The contributor is male · the affected area is the arm and back of the hand · the contributor reports burning, bleeding, enlargement, darkening, itching, pain and bothersome appearance · the patient described the issue as a growth or mole · self-reported Fitzpatrick III · texture is reported as fluid-filled, raised or bumpy and rough or flaky · the photograph was taken at an angle · reported duration is three to twelve months: 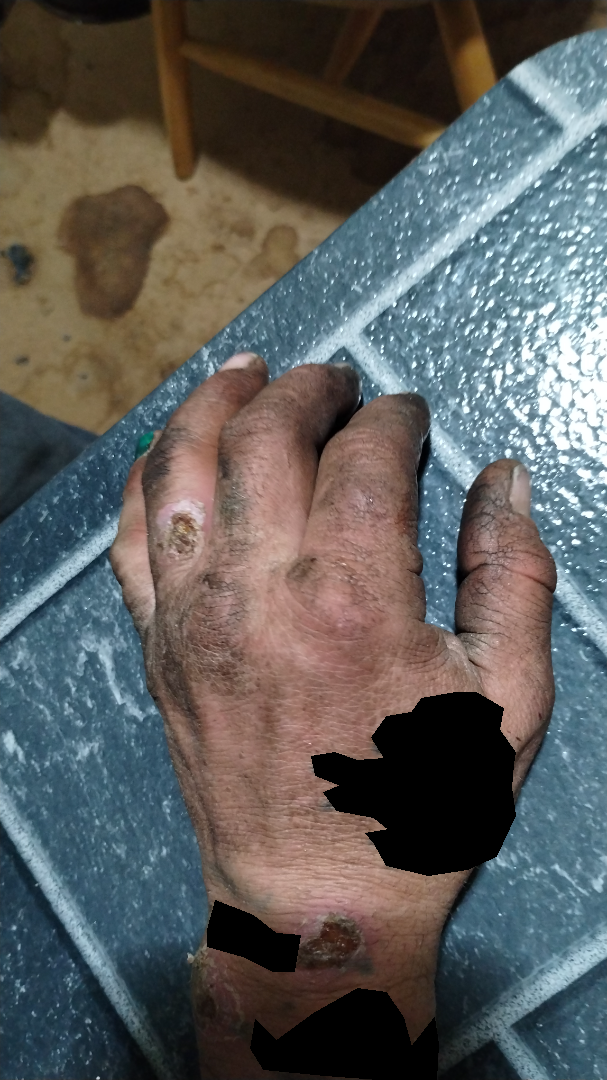assessment = could not be assessed